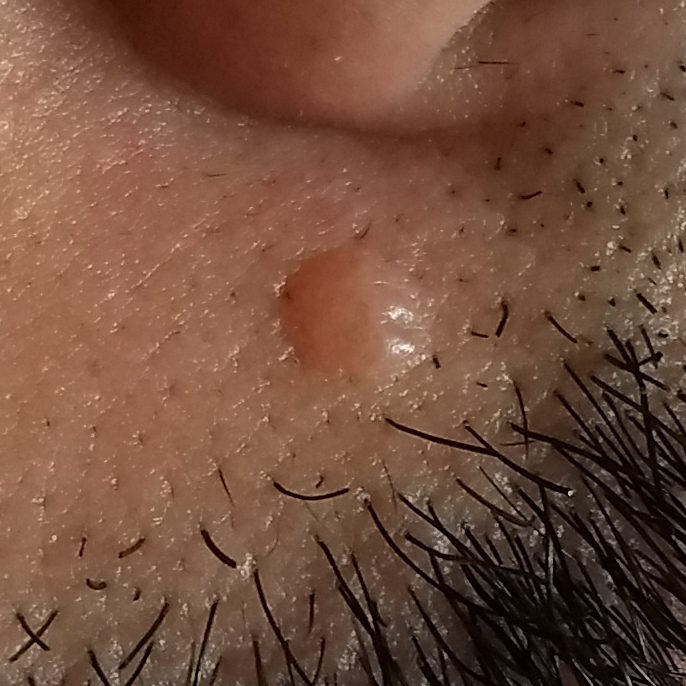Patient and lesion: The lesion involves the face. Conclusion: Diagnosed by dermatologist consensus as a benign skin lesion — a nevus.